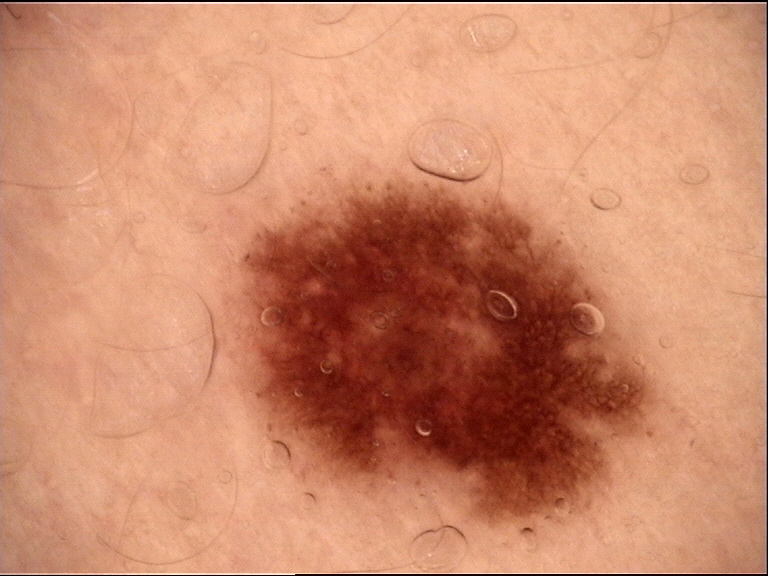Findings:
A dermoscopic photograph of a skin lesion.
Impression:
Labeled as a dysplastic junctional nevus.